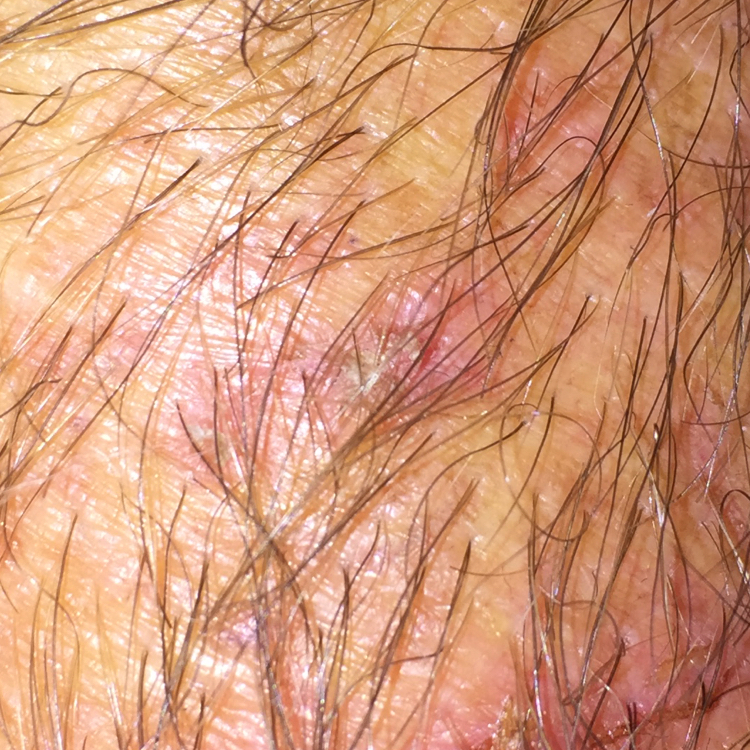{"image": "clinical photo", "patient": {"age": 40}, "lesion_location": "an arm", "diagnosis": {"name": "actinic keratosis", "code": "ACK", "malignancy": "indeterminate", "confirmation": "clinical consensus"}}